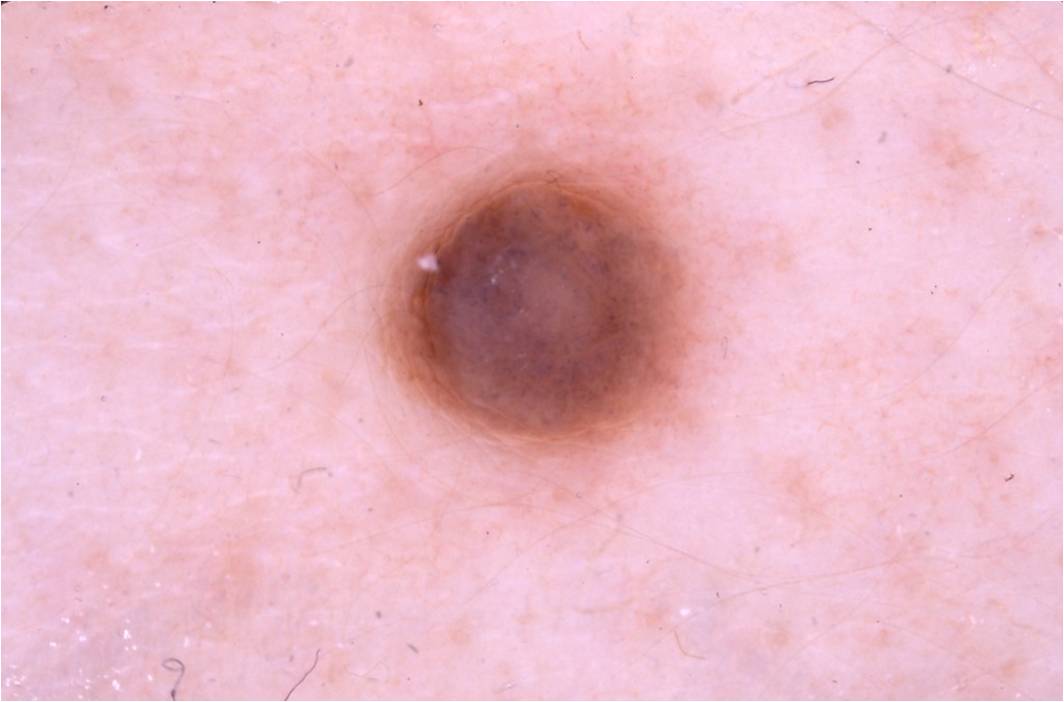A dermoscopic view of a skin lesion. A male subject about 5 years old. Dermoscopic assessment notes no negative network, globules, milia-like cysts, pigment network, or streaks. The lesion occupies roughly 10% of the field. As (left, top, right, bottom), the lesion is located at bbox(381, 157, 713, 448). The clinical diagnosis was a melanocytic nevus.